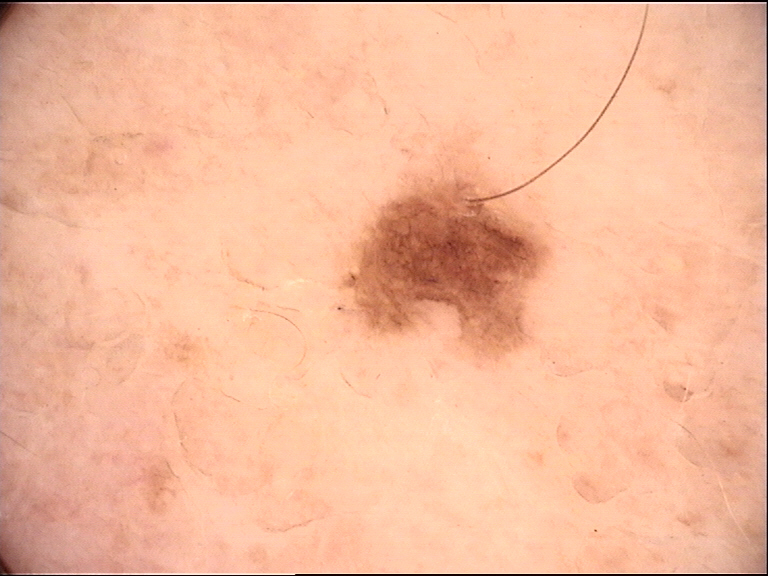Consistent with a dysplastic junctional nevus.